A female patient age 64. A clinical close-up photograph of a skin lesion: 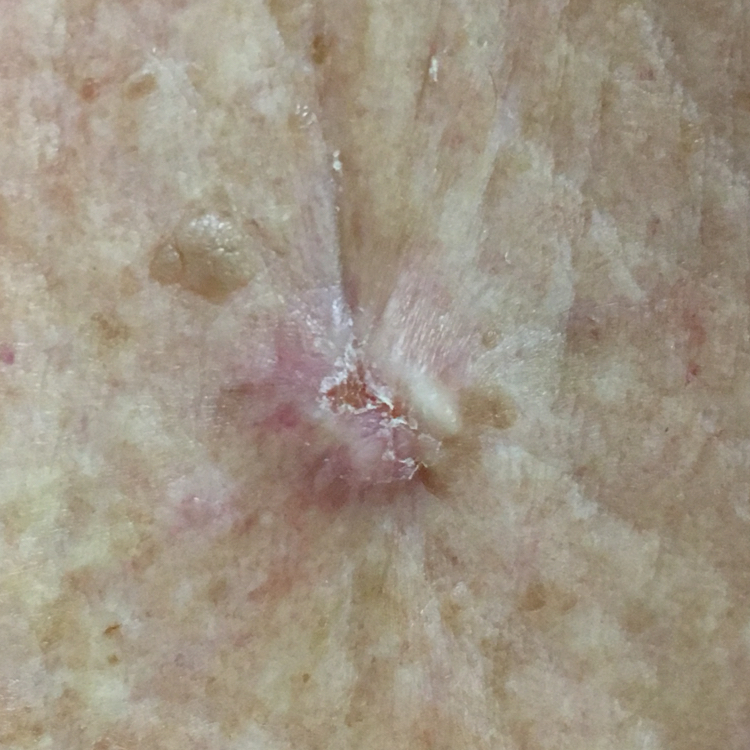Case:
• region: the chest
• pathology: basal cell carcinoma (biopsy-proven)